Dermoscopy of a skin lesion: 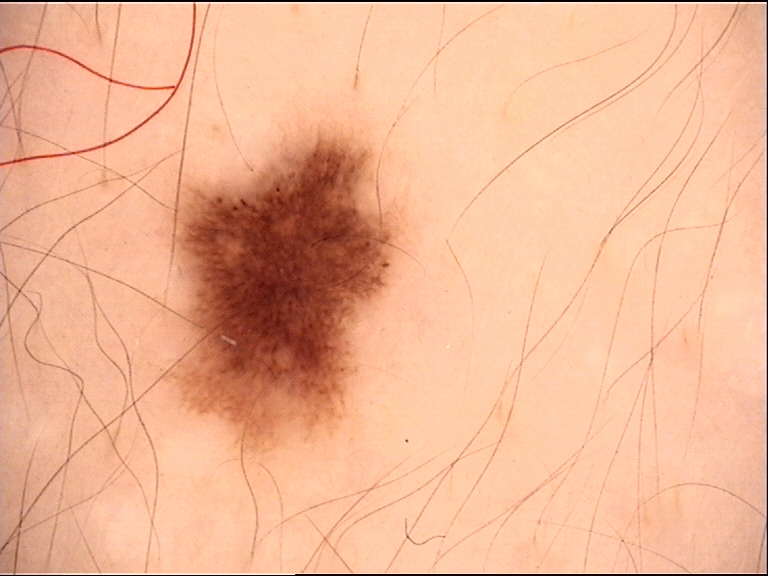diagnostic label: dysplastic junctional nevus (expert consensus).